A skin lesion imaged with a dermatoscope · the patient is a male about 15 years old: 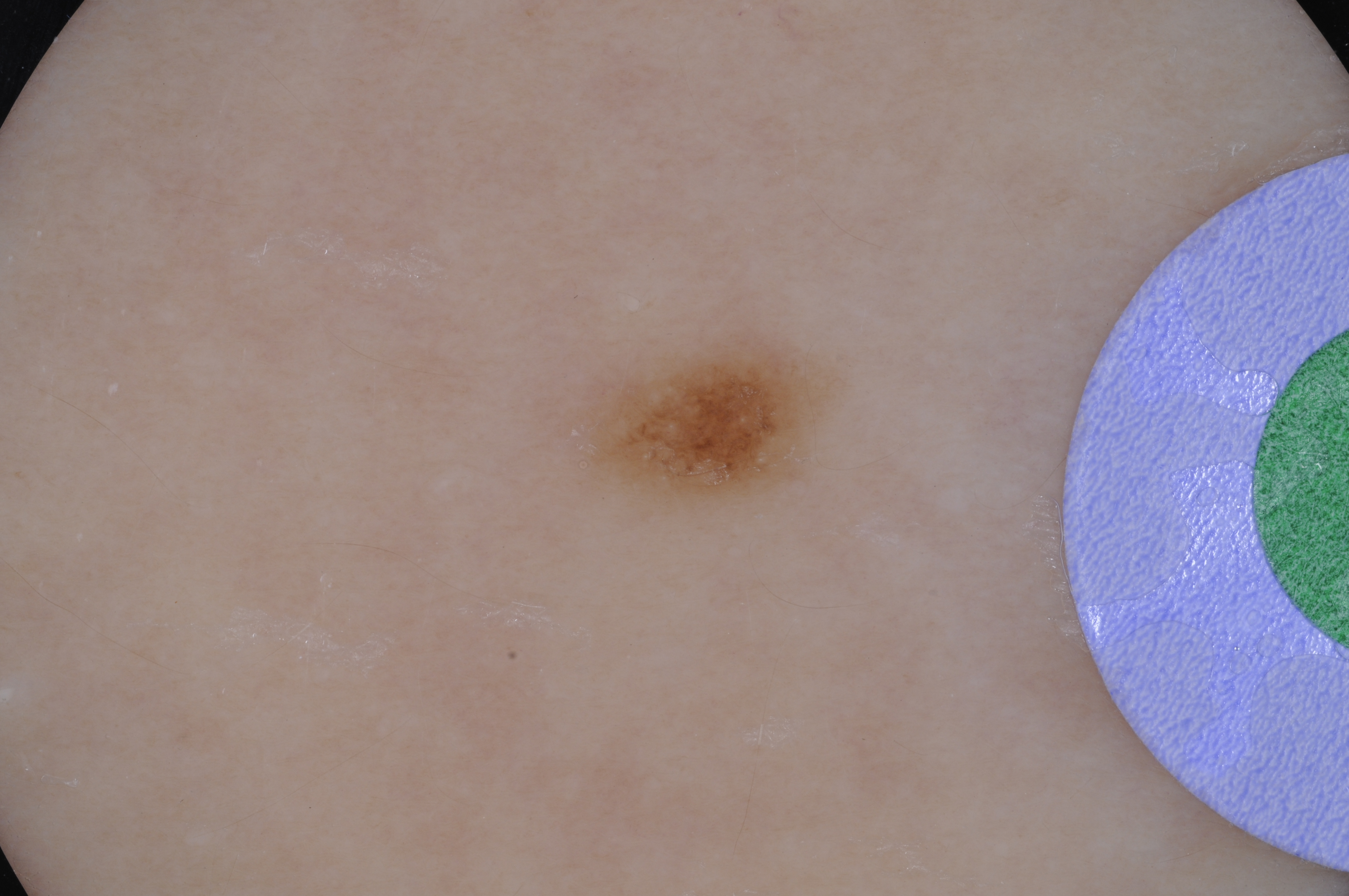The lesion is small relative to the field of view. As (left, top, right, bottom), the lesion occupies the region (552, 334, 857, 509). Dermoscopic review identifies milia-like cysts; no streaks, globules, pigment network, or negative network. Consistent with a melanocytic nevus, a benign lesion.